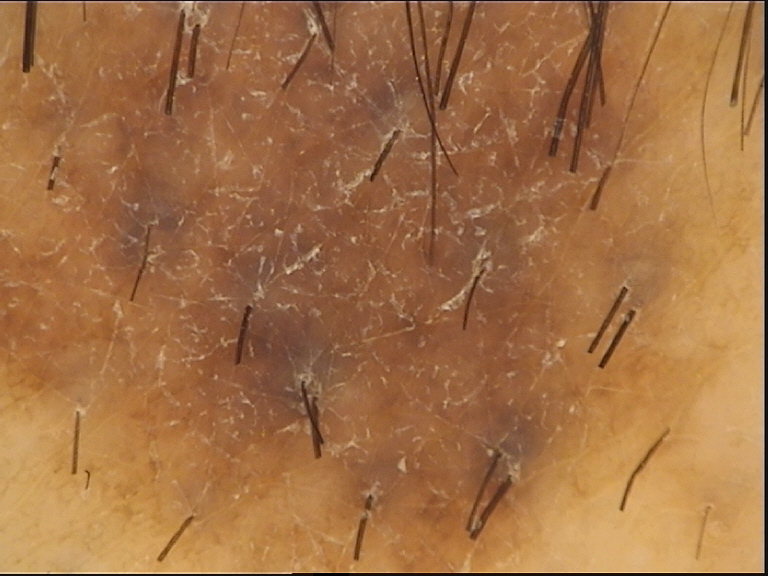Dermoscopy of a skin lesion. Consistent with a dysplastic compound nevus.